A clinical close-up photograph of a skin lesion; a subject in their 70s: 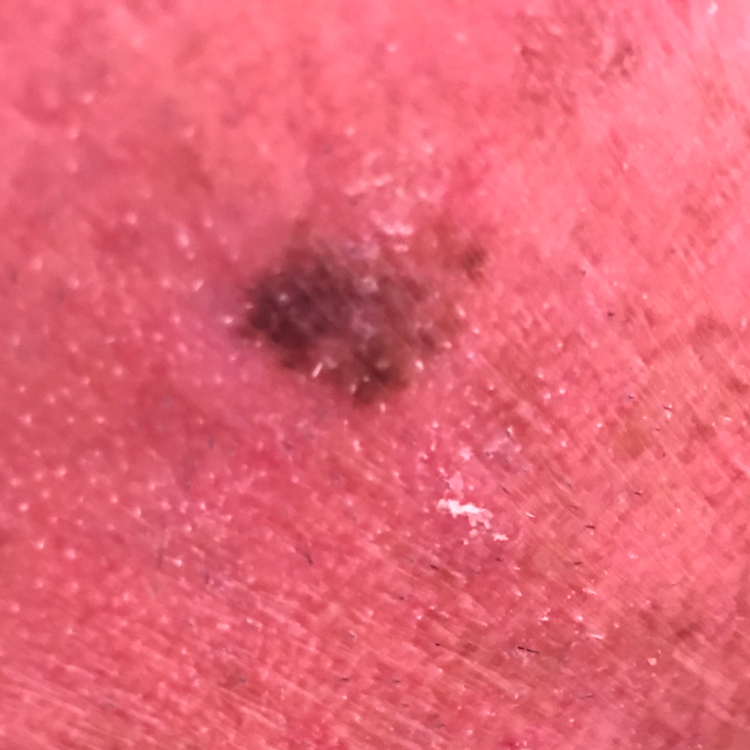Located on the face.
The patient reports no symptoms.
The clinical impression was a seborrheic keratosis.